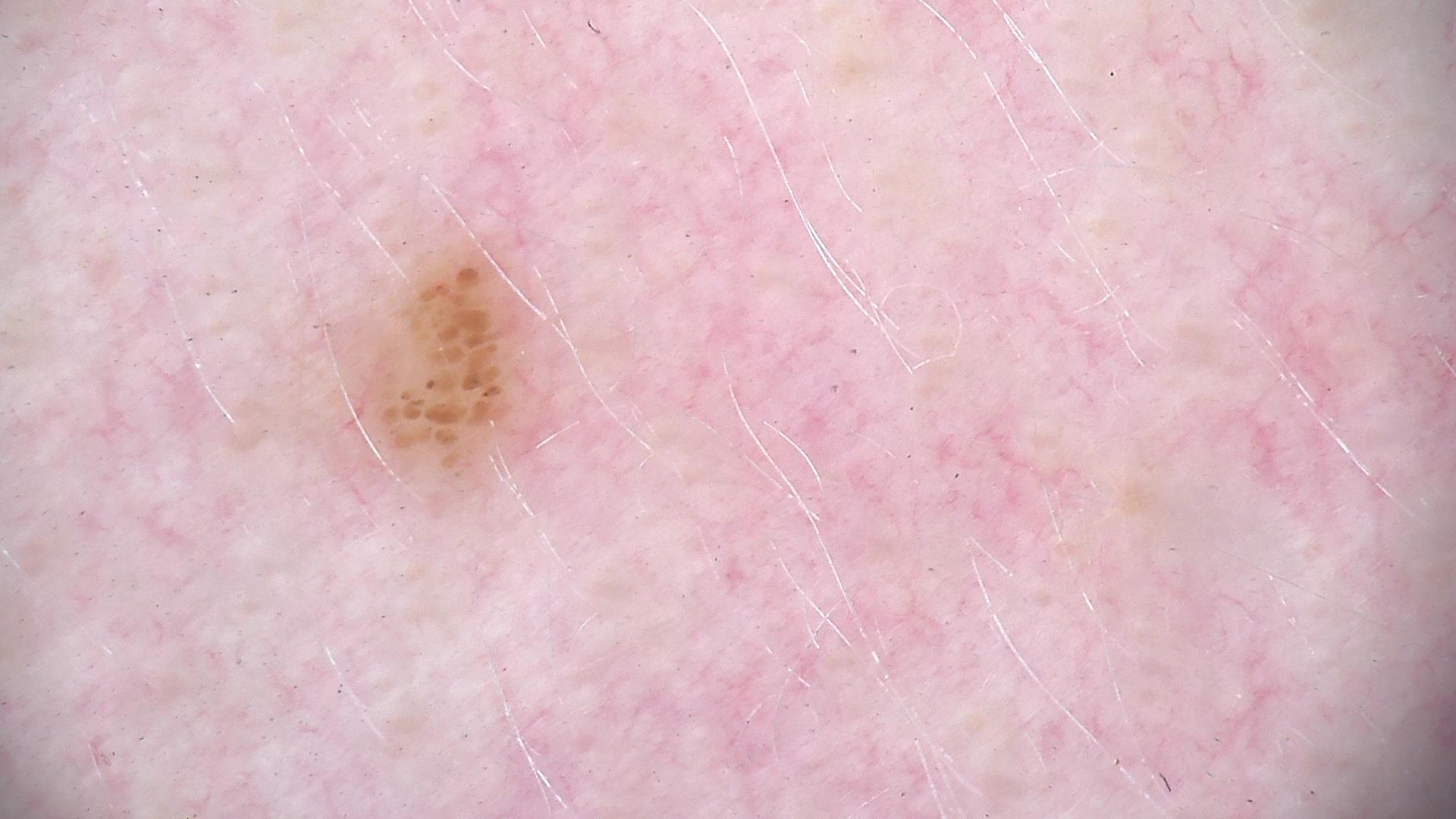modality: dermatoscopy, subtype: banal, diagnosis: junctional nevus (expert consensus).